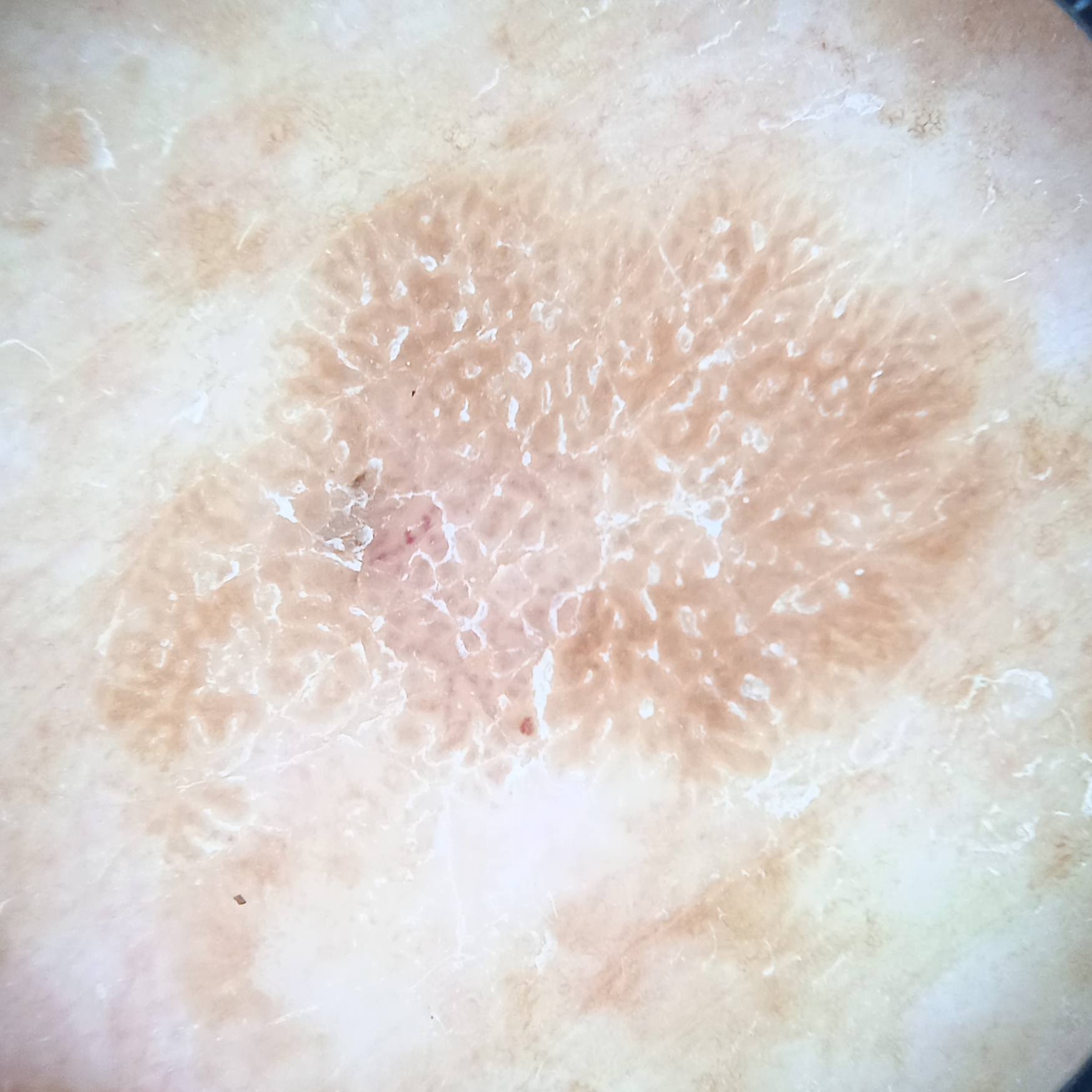modality = dermatoscopic image; subject = male, age 73; relevant history = a personal history of cancer; diagnostic label = seborrheic keratosis (dermatologist consensus).